A female patient, roughly 60 years of age. Dermoscopy of a skin lesion — 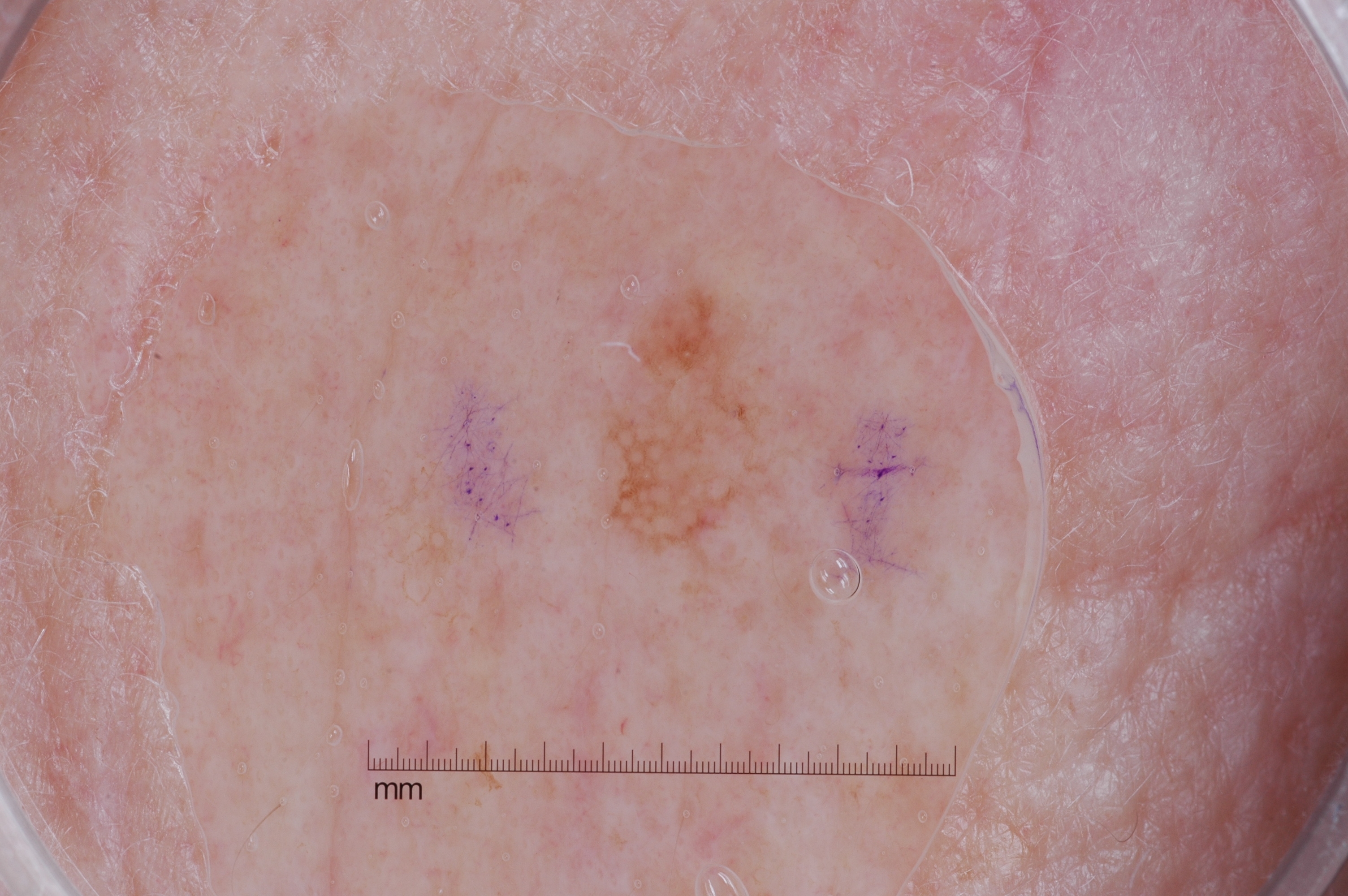location — left=574, top=278, right=834, bottom=567 | dermoscopic pattern — milia-like cysts; absent: streaks, pigment network, and negative network | diagnosis — a melanocytic nevus, a benign lesion.